The lesion involves the head or neck · this image was taken at a distance · the condition has been present for since childhood · the contributor is a female aged 40–49 · self-categorized by the patient as acne · the patient notes the lesion is raised or bumpy: 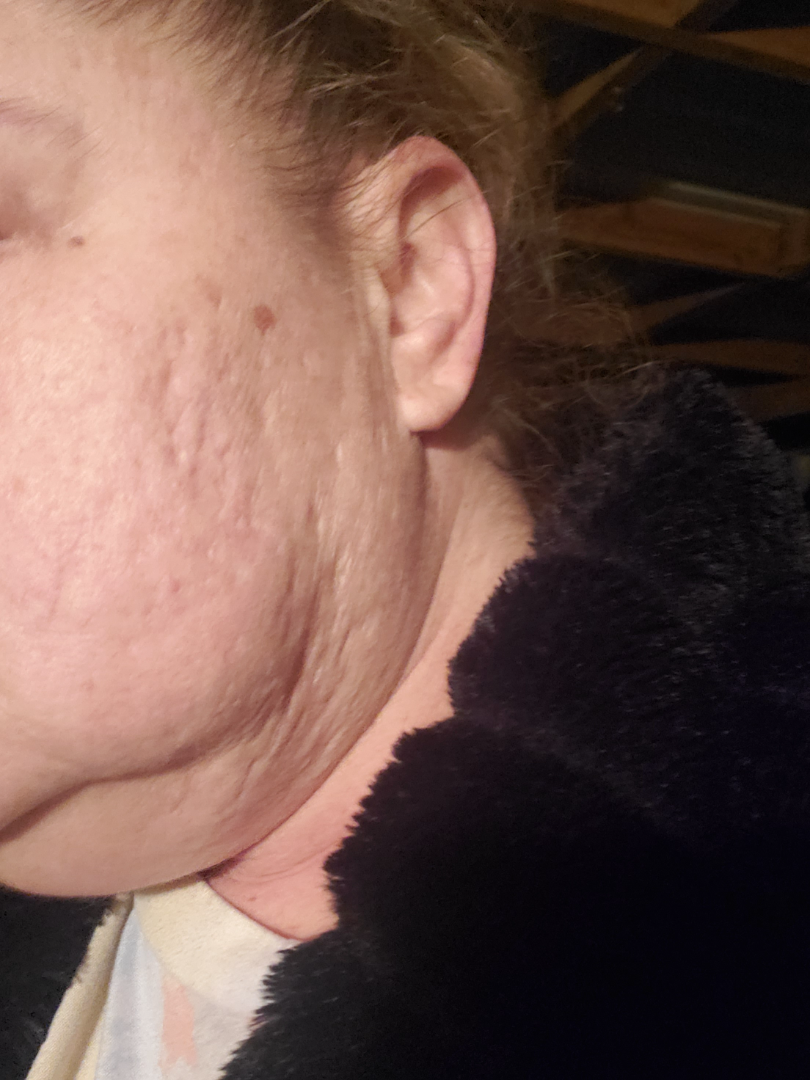On photographic review by a dermatologist, consistent with Scar Condition.